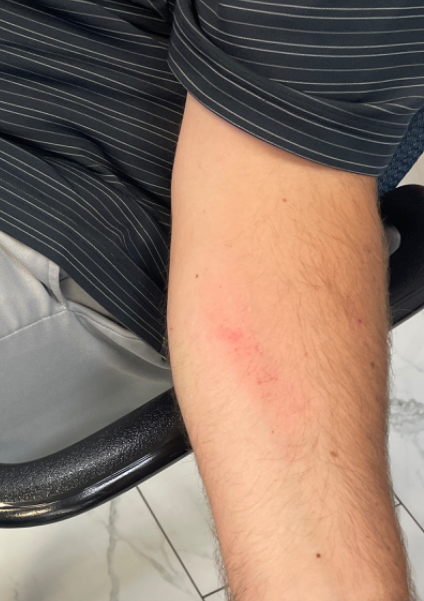Q: Could the case be diagnosed?
A: indeterminate
Q: What is the framing?
A: at a distance
Q: Anatomic location?
A: arm
Q: Age and sex?
A: male, age 30–39